A dermatoscopic image of a skin lesion.
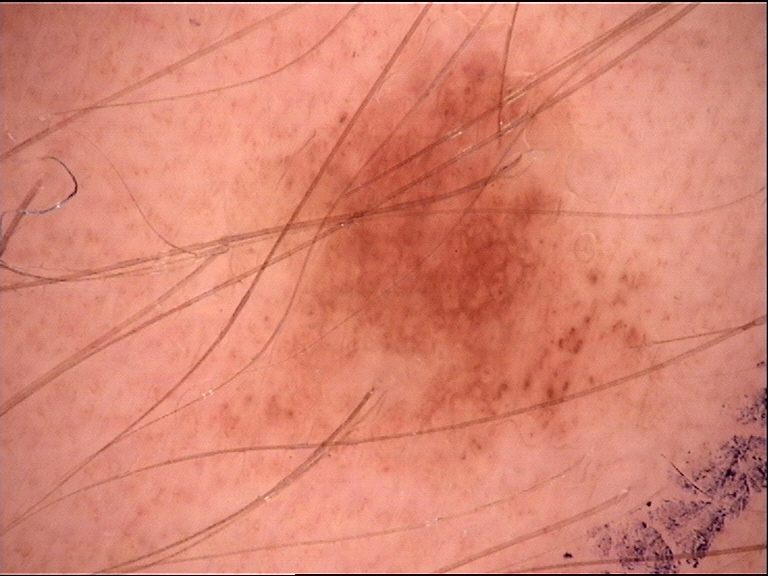Findings:
* assessment: dysplastic junctional nevus (expert consensus)